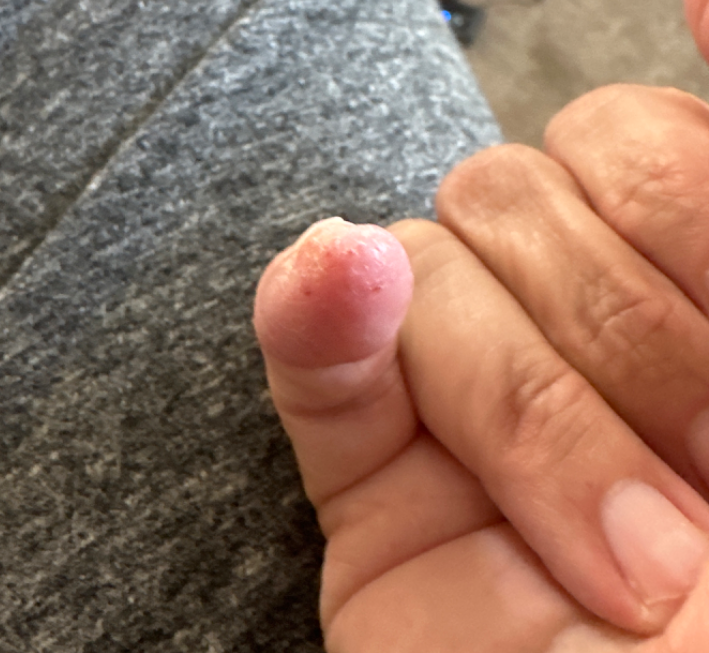  body_site: back of the hand
  symptoms:
    - pain
    - itching
    - burning
    - bleeding
  shot_type: close-up
  texture: rough or flaky
  patient_category: a rash
  systemic_symptoms: none reported
  patient: female, age 50–59
  duration: one to three months
  differential:
    leading:
      - Acute-on-chronic dyshidrotic eczema of hands